Present for more than five years · Fitzpatrick IV · the patient considered this hair loss · the patient reported no systemic symptoms · the lesion is described as rough or flaky and raised or bumpy · this image was taken at a distance · reported lesion symptoms include bleeding, pain, itching and burning · located on the leg:
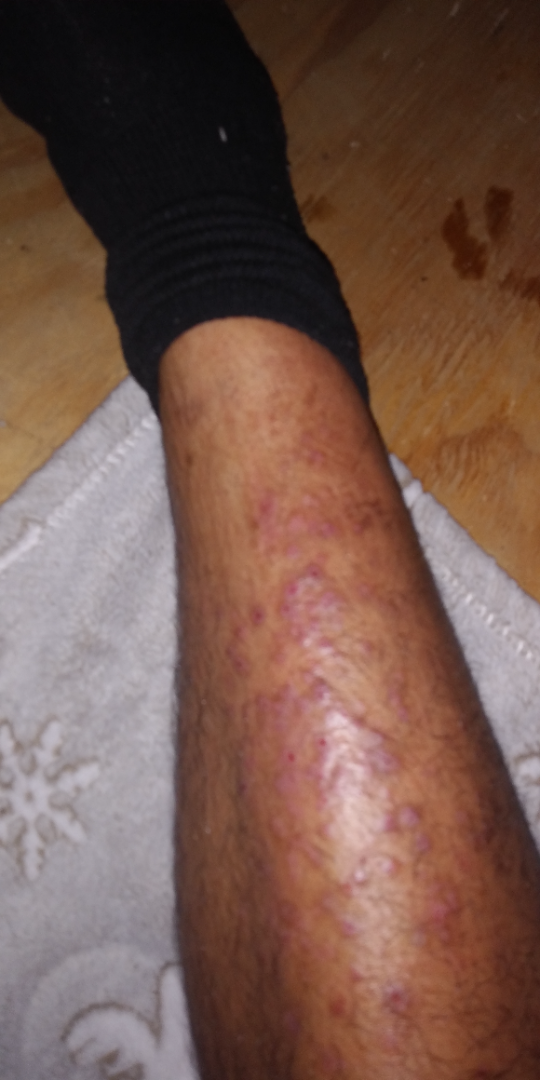Three independent reviewers: the differential, in no particular order, includes Lichen planus/lichenoid eruption and Prurigo nodularis; less probable is Drug Rash.